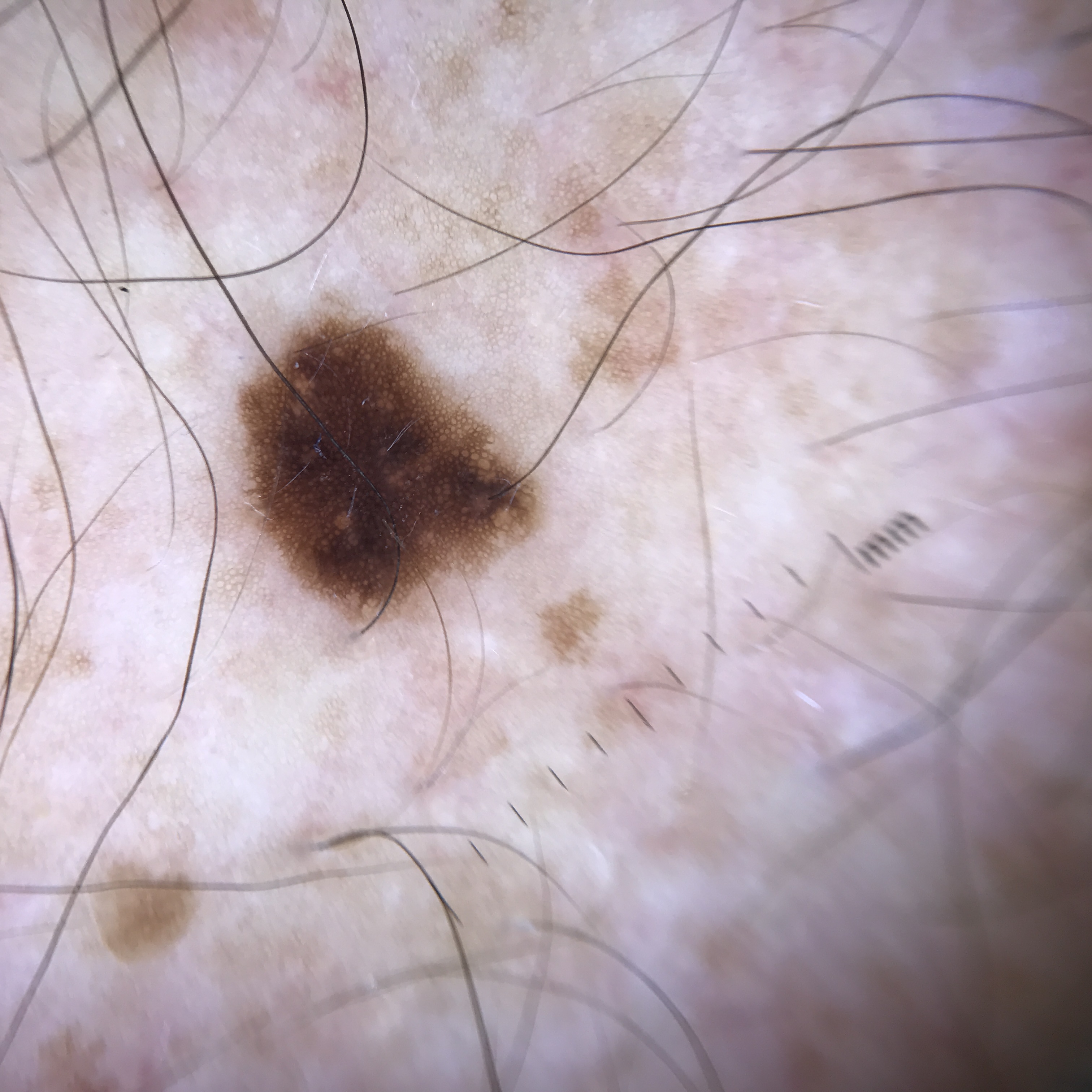The morphology is that of a banal lesion.
The diagnostic label was a junctional nevus.